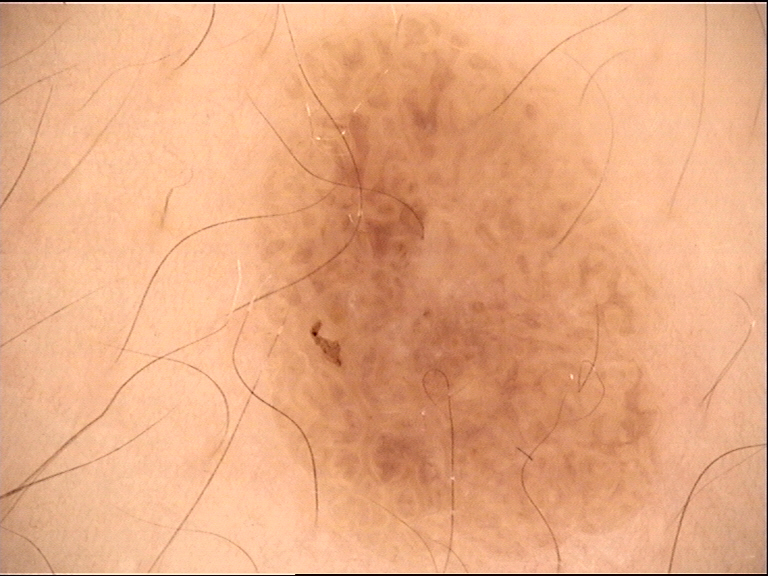A dermatoscopic image of a skin lesion. The architecture is that of a keratinocytic lesion. Diagnosed as a benign lesion — a seborrheic keratosis.